A dermoscopic photograph of a skin lesion:
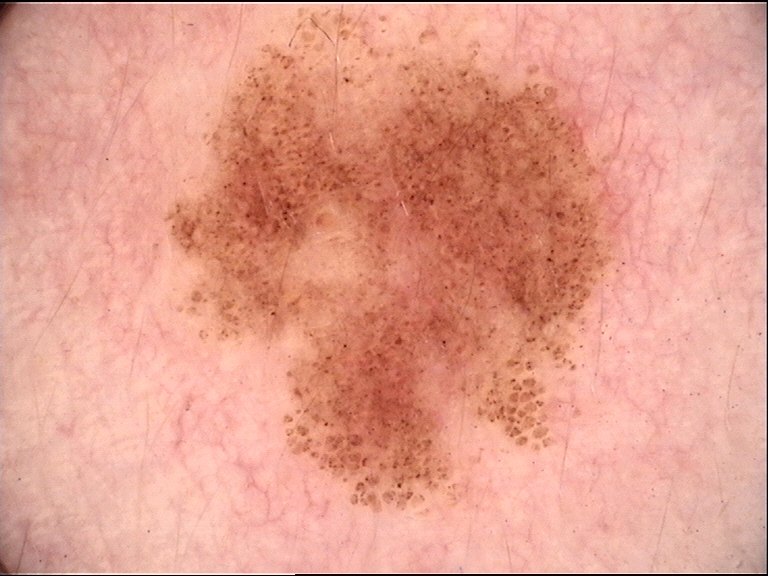Diagnosed as a dysplastic junctional nevus.